A close-up photograph; the affected area is the leg — 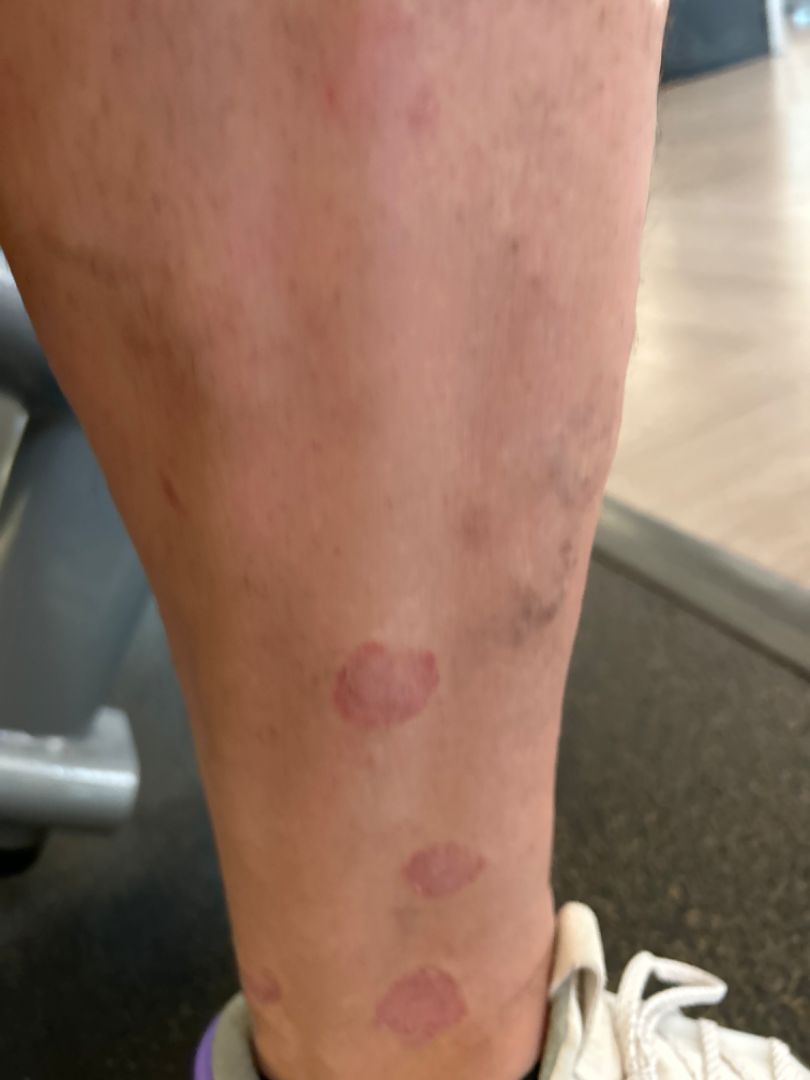Q: What is the differential diagnosis?
A: favoring Eczema; the differential also includes Parapsoriasis; also raised was Psoriasis